A dermoscopic close-up of a skin lesion:
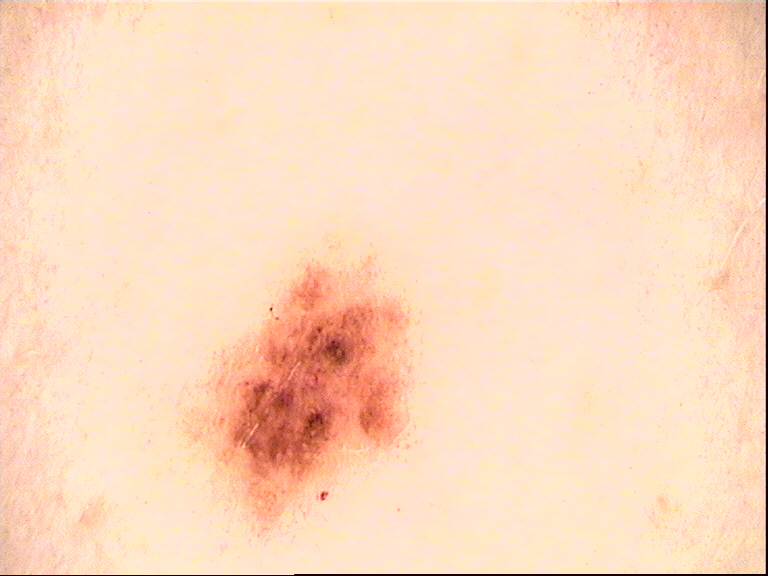Labeled as a dysplastic junctional nevus.